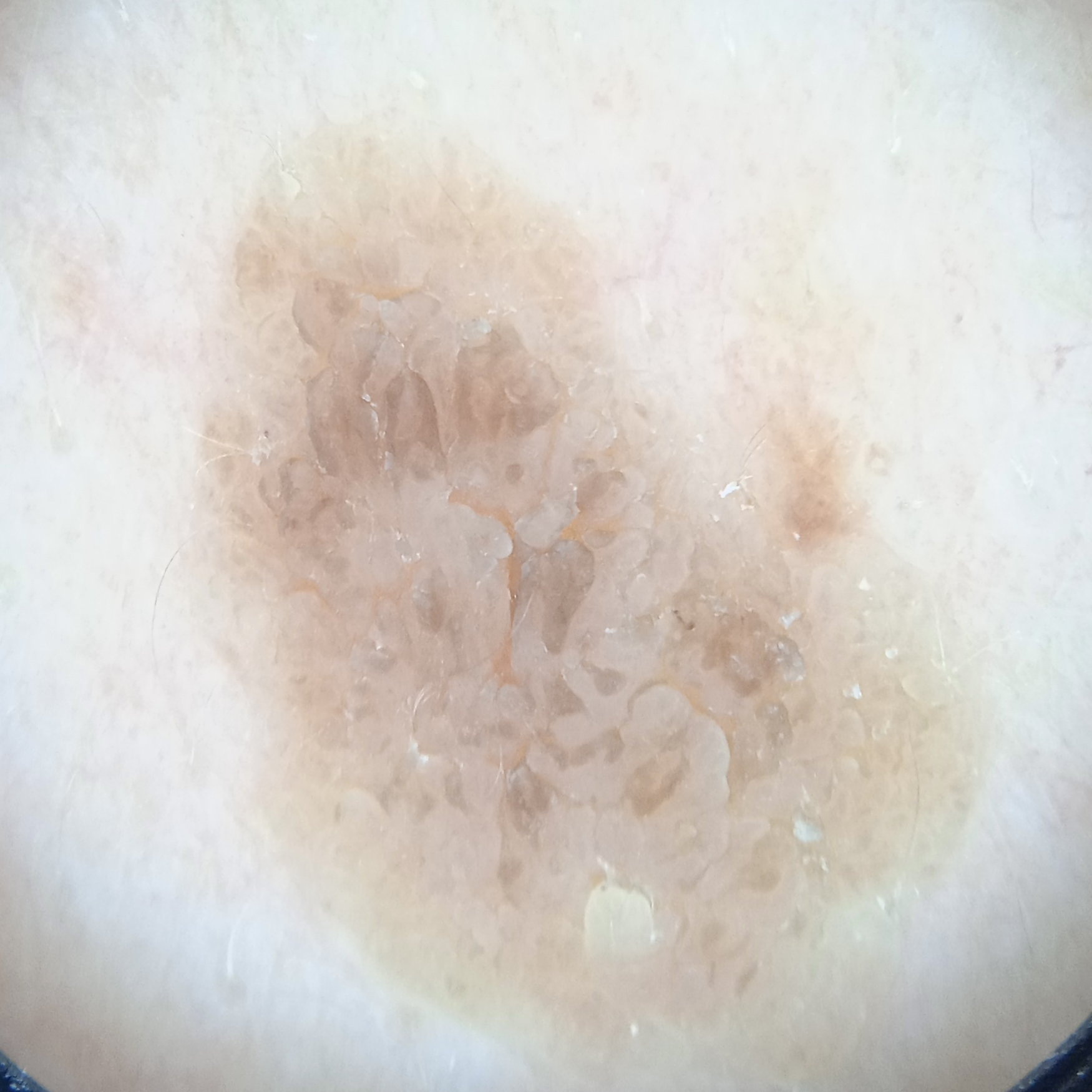Findings:
* patient: male, 64 years of age
* nevus count: few melanocytic nevi overall
* referral: clinical suspicion of seborrheic keratosis
* sun reaction: skin tans without first burning
* site: the back
* assessment: seborrheic keratosis (dermatologist consensus)